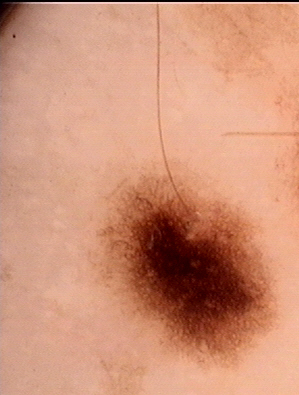image type: dermoscopy | category: banal | class: junctional nevus (expert consensus).